The contributor is 30–39, female · the head or neck is involved · this image was taken at a distance: 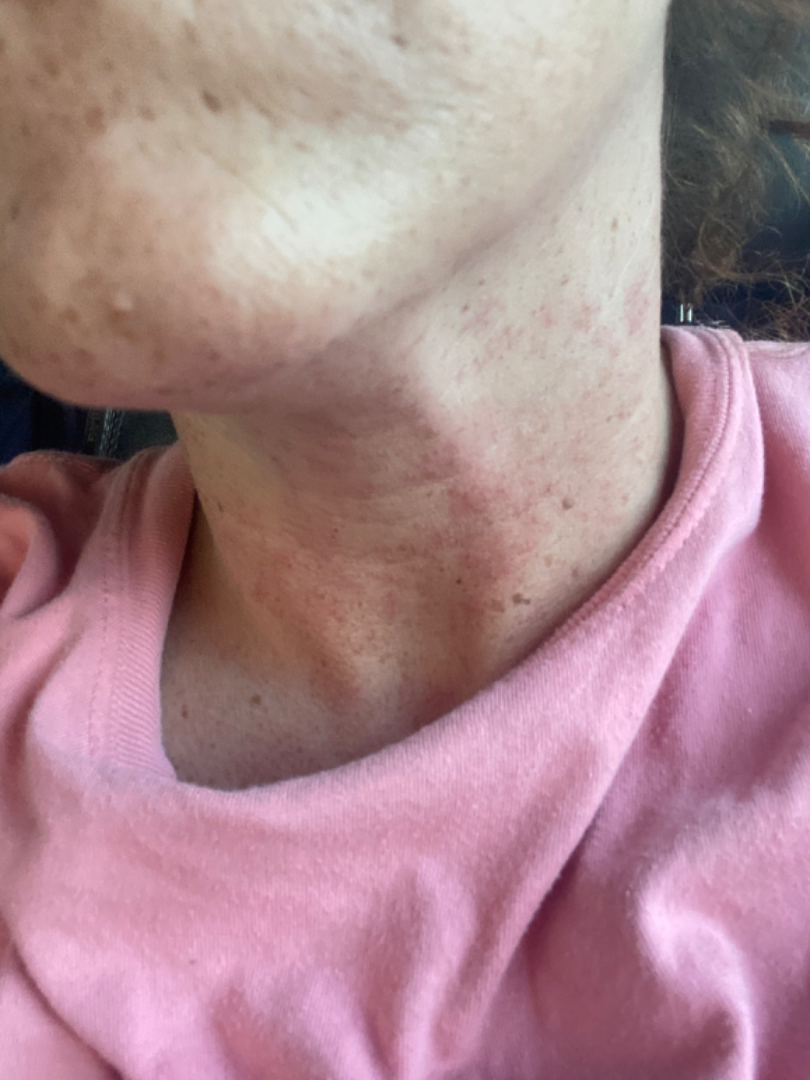self-categorized as — a rash | surface texture — flat, raised or bumpy and rough or flaky | duration — less than one week | impression — most consistent with Acne; also on the differential is Folliculitis; a remote consideration is Allergic Contact Dermatitis.